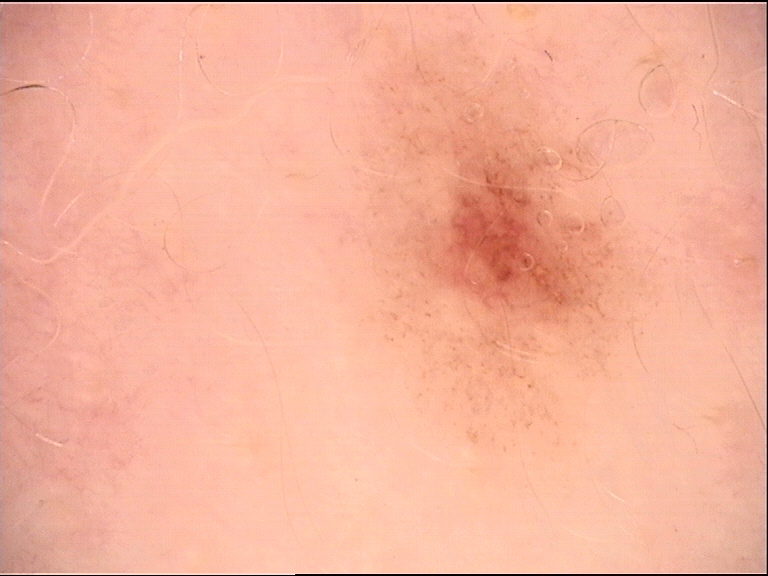A dermoscopic close-up of a skin lesion. Consistent with a dysplastic junctional nevus.